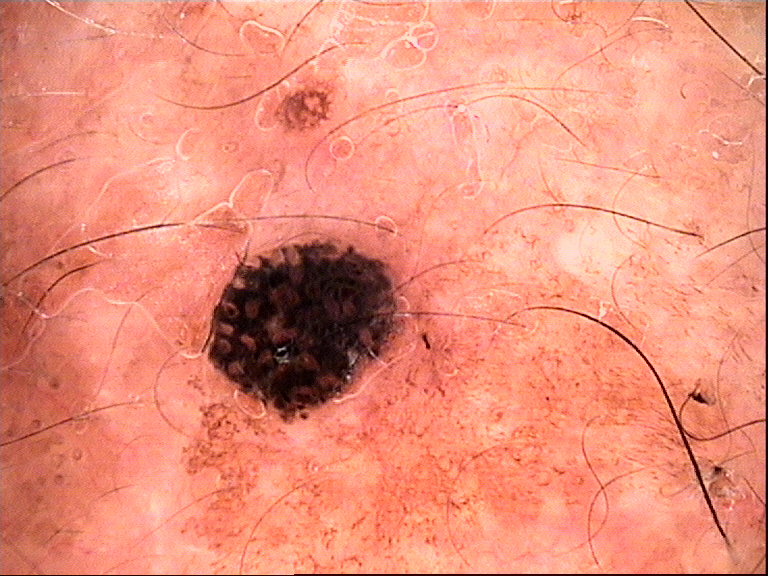Case:
• image: dermoscopy
• diagnostic label: seborrheic keratosis (expert consensus)